A dermatoscopic image of a skin lesion:
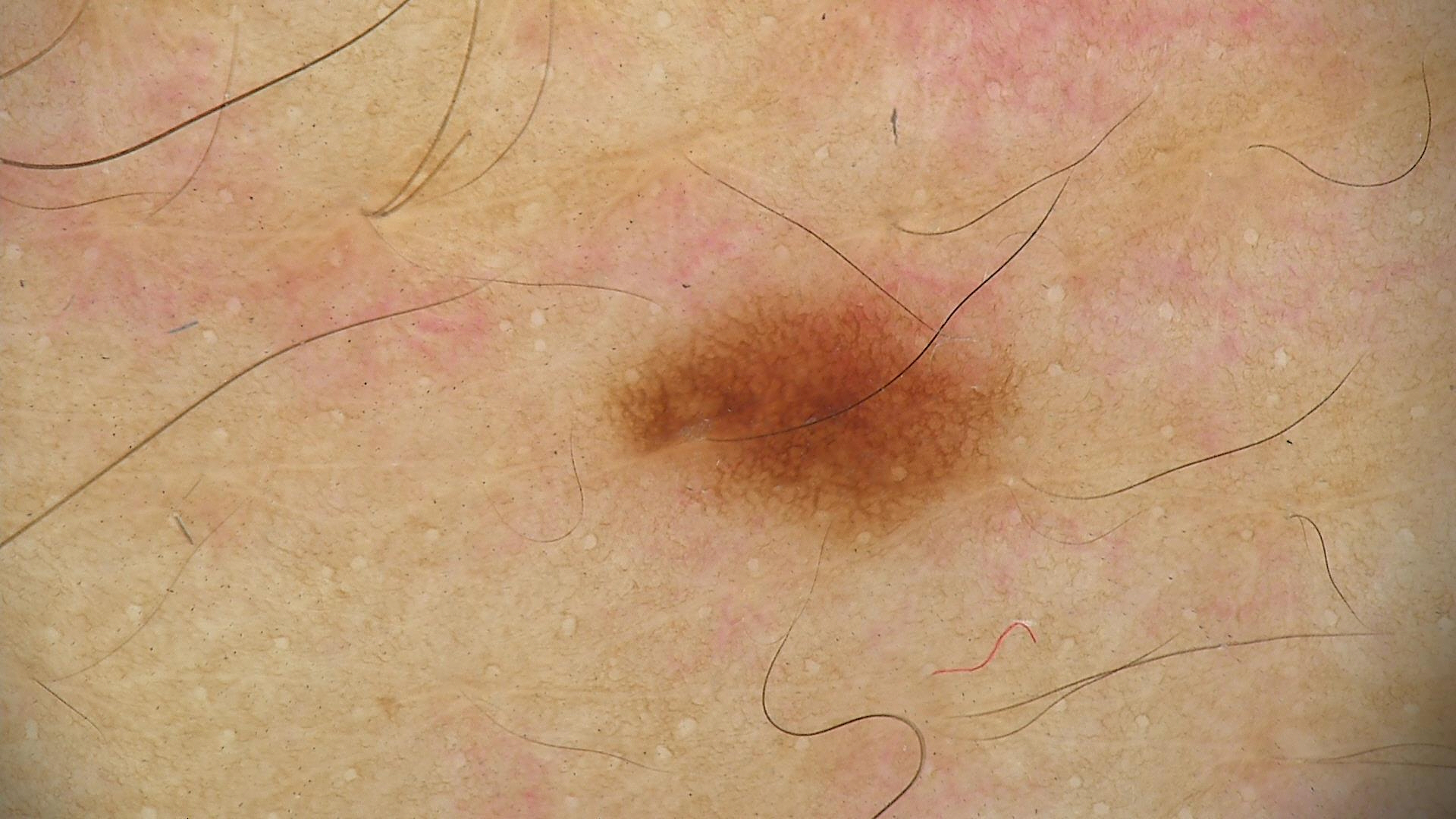Q: What is the diagnosis?
A: dysplastic junctional nevus (expert consensus)